A dermatoscopic image of a skin lesion: 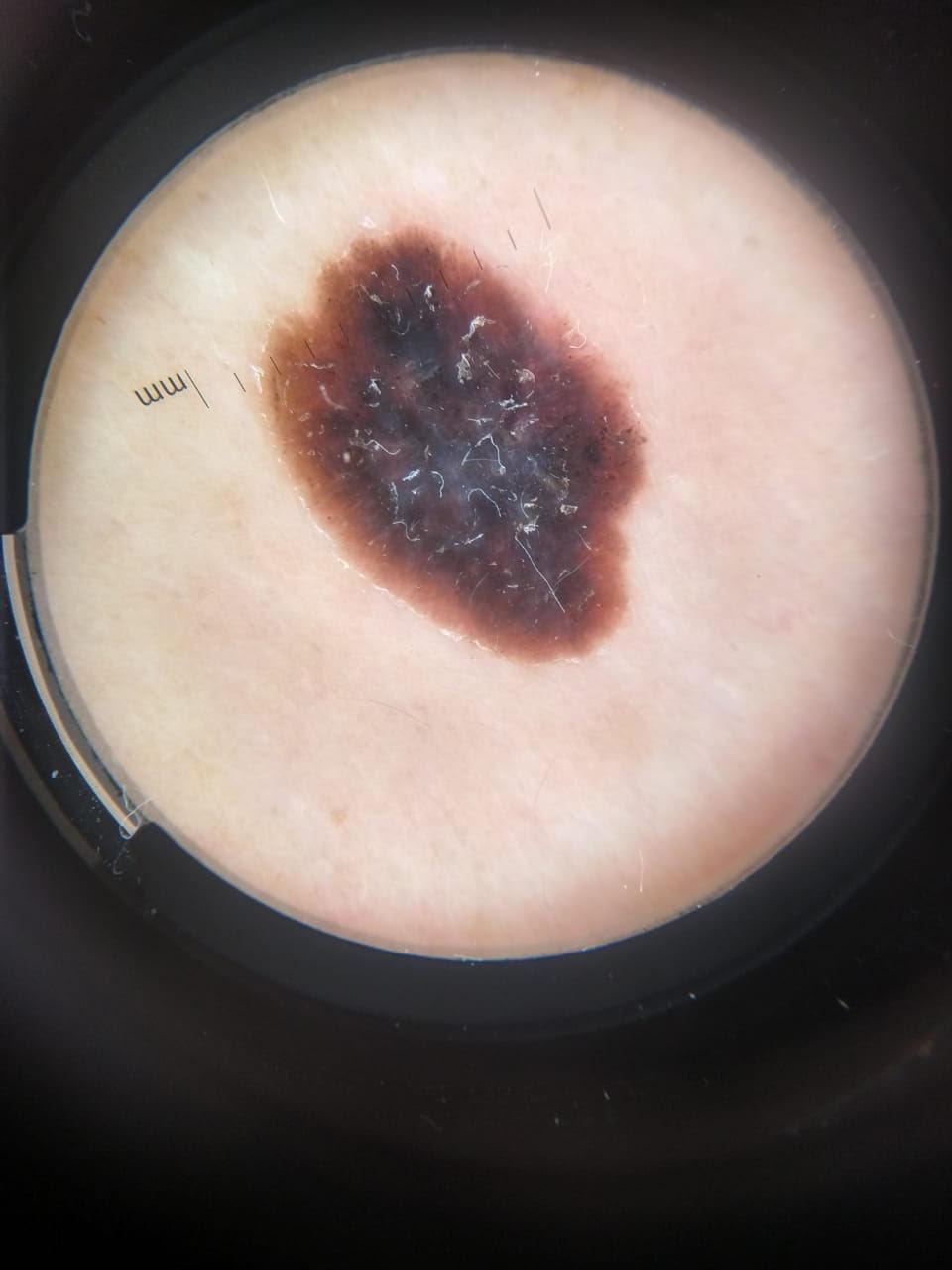Histopathological examination showed a melanoma.